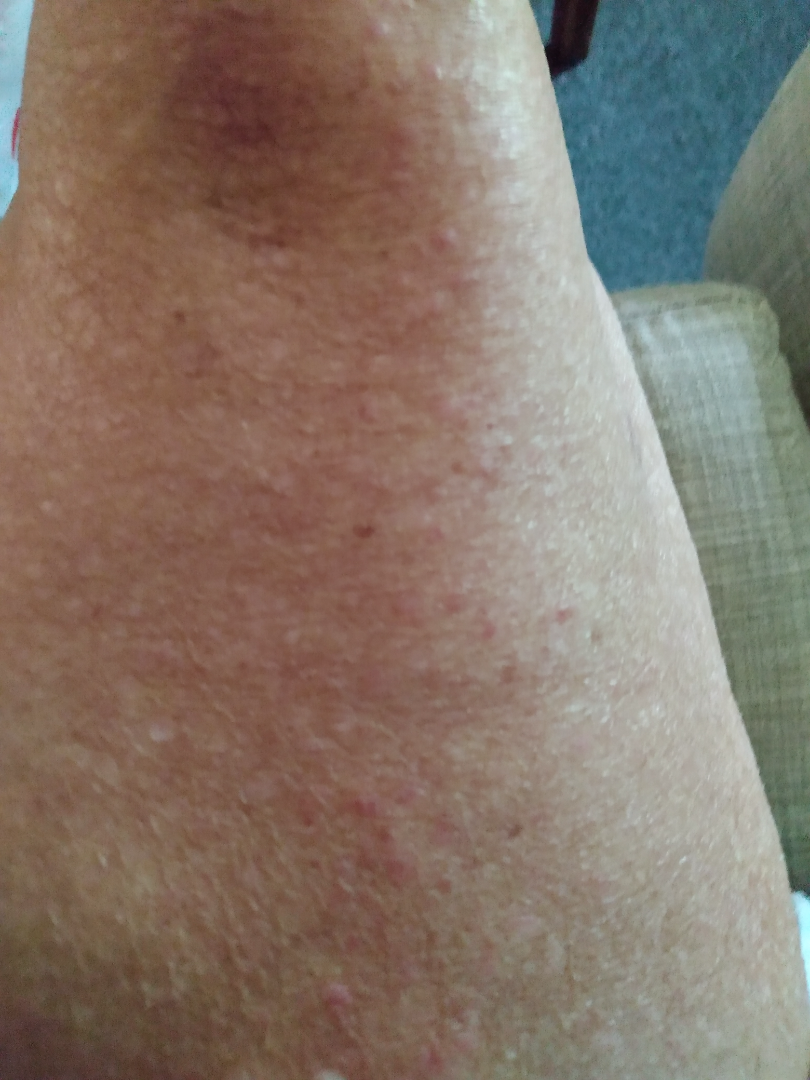assessment = ungradable on photographic review | affected area = leg, front of the torso, arm and back of the torso | shot type = close-up | lesion symptoms = itching, pain and burning | patient describes the issue as = a rash | subject = female, age 60–69 | described texture = raised or bumpy.